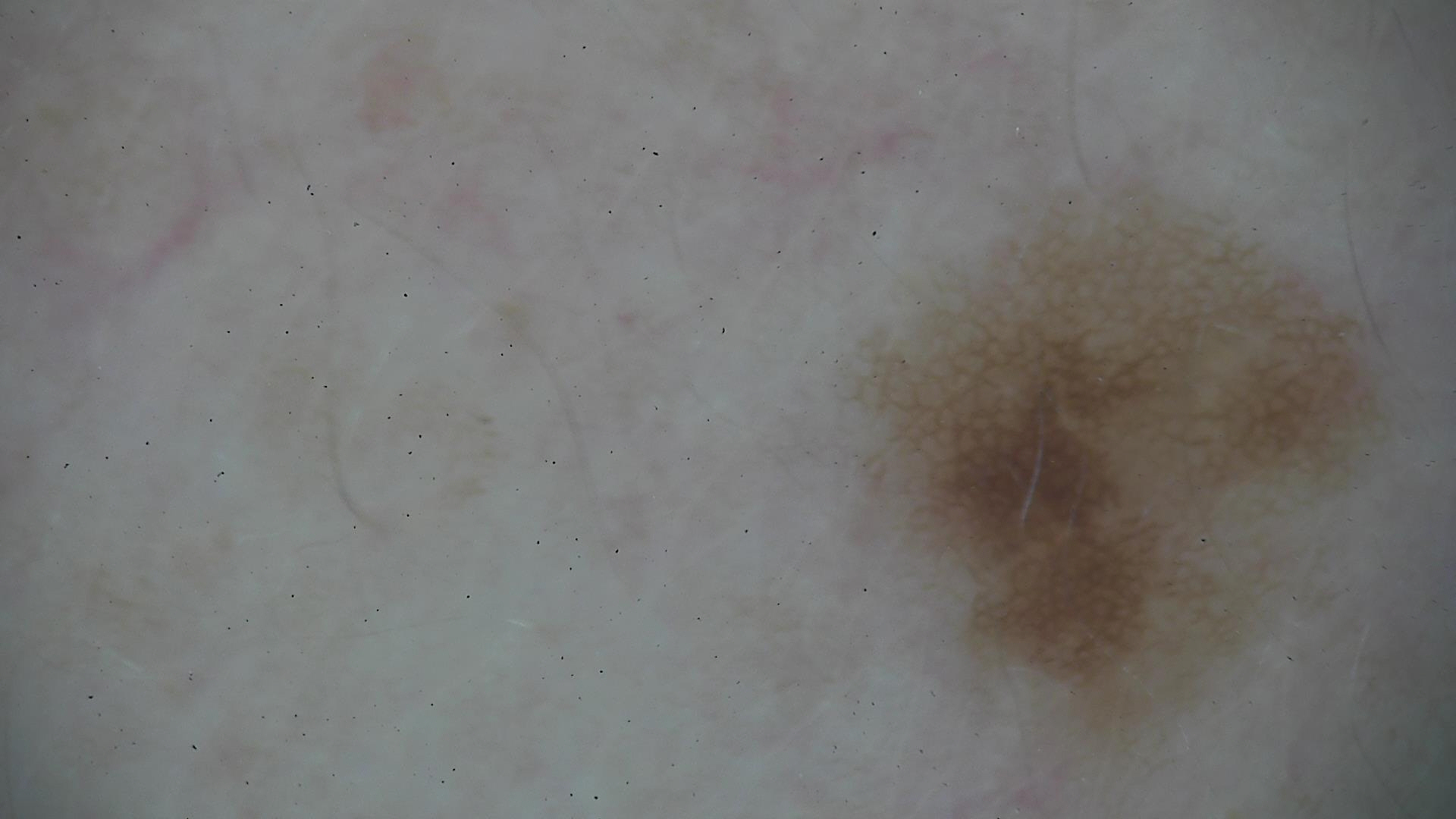A dermoscopic close-up of a skin lesion.
Classified as a benign lesion — a dysplastic junctional nevus.